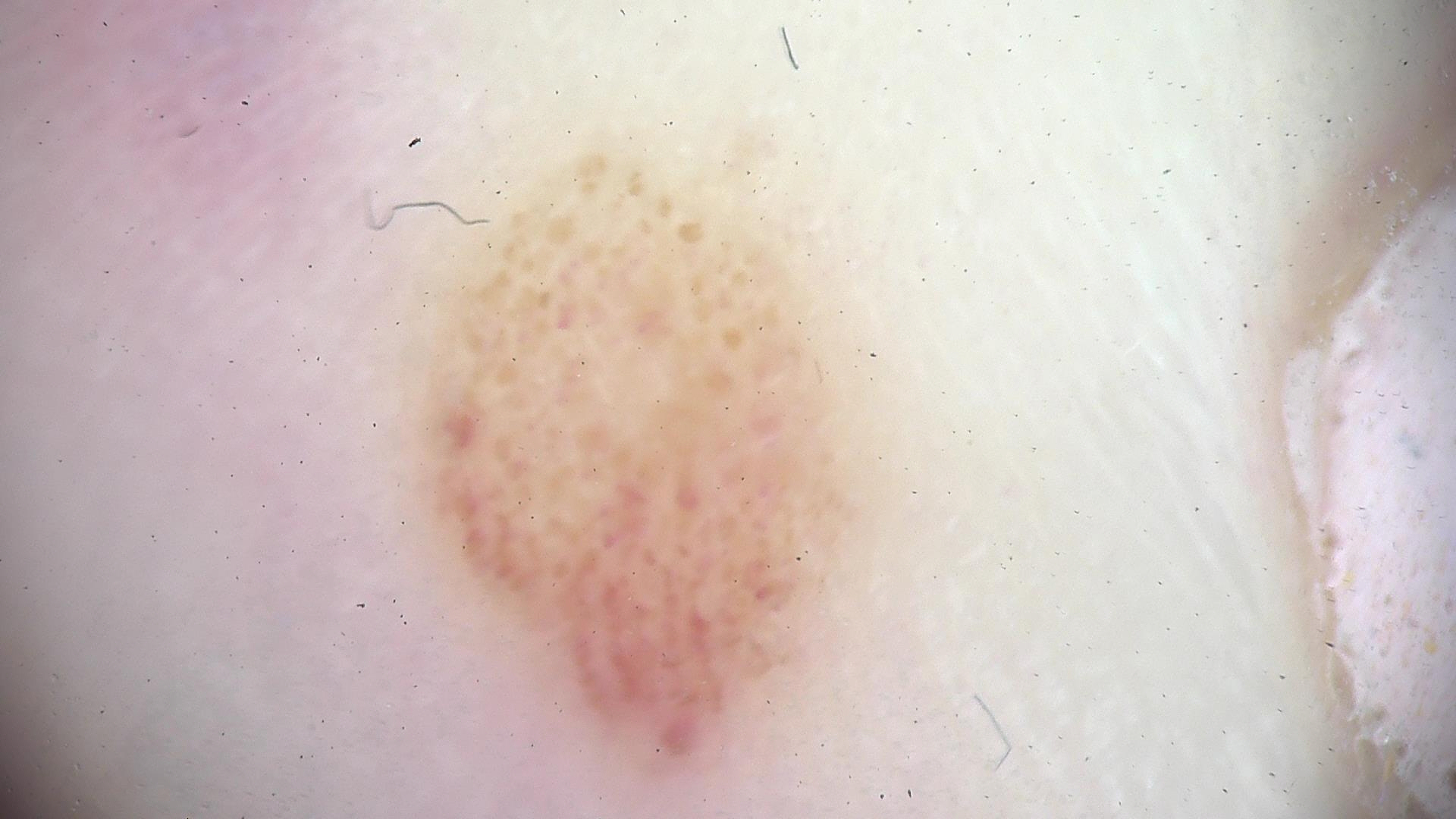assessment: acral dysplastic compound nevus (expert consensus)